A male patient 68 years of age · a clinical photo of a skin lesion taken with a smartphone · the chart records pesticide exposure, prior malignancy (patient or family), prior skin cancer (patient or family), and no alcohol use:
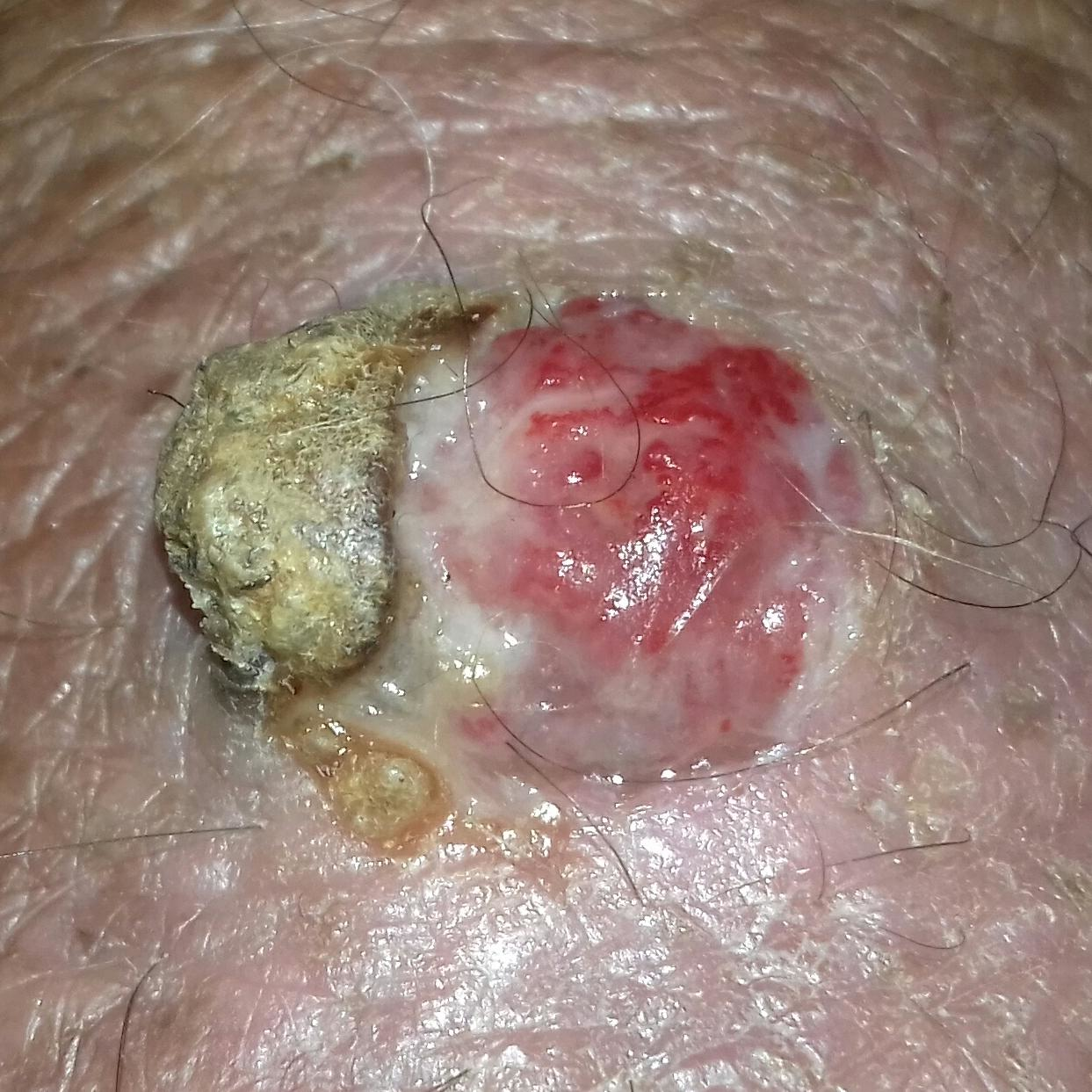{
  "lesion_size": {
    "diameter_1_mm": 11.0,
    "diameter_2_mm": 7.0
  },
  "symptoms": {
    "present": [
      "bleeding",
      "elevation",
      "growth",
      "change in appearance",
      "pain",
      "itching"
    ]
  },
  "diagnosis": {
    "name": "squamous cell carcinoma",
    "code": "SCC",
    "malignancy": "malignant",
    "confirmation": "histopathology"
  }
}